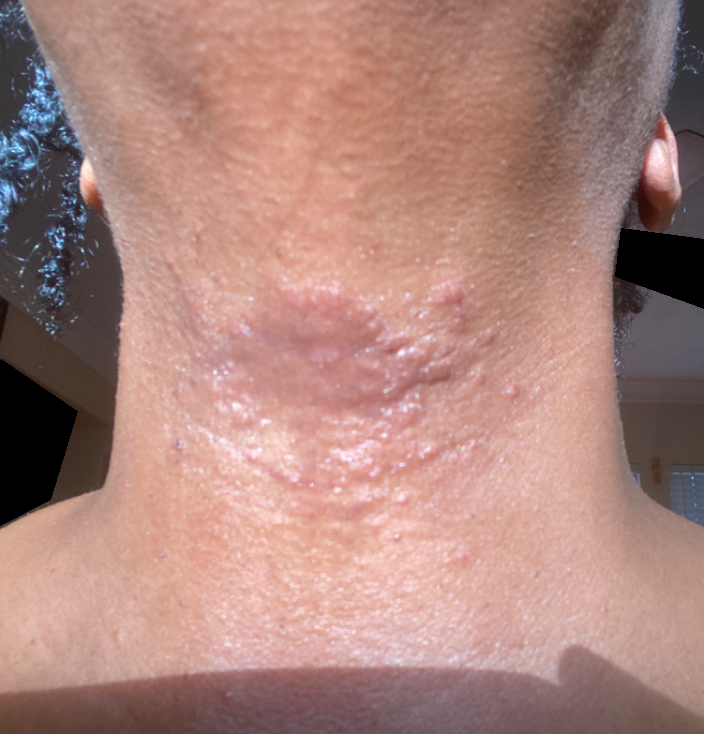Findings:
- duration · one to four weeks
- other reported symptoms · none reported
- contributor · female, age 50–59
- lesion symptoms · enlargement, bothersome appearance, darkening and itching
- patient's own categorization · skin that appeared healthy to them
- shot type · close-up
- body site · head or neck
- differential · Allergic Contact Dermatitis (possible); Cutaneous sarcoidosis (possible); Eczema (lower probability); Drug Rash (lower probability); Lichenoid myxedema (lower probability)